The patient was assessed as skin type II. The chart records a previous melanoma. A male patient roughly 75 years of age.
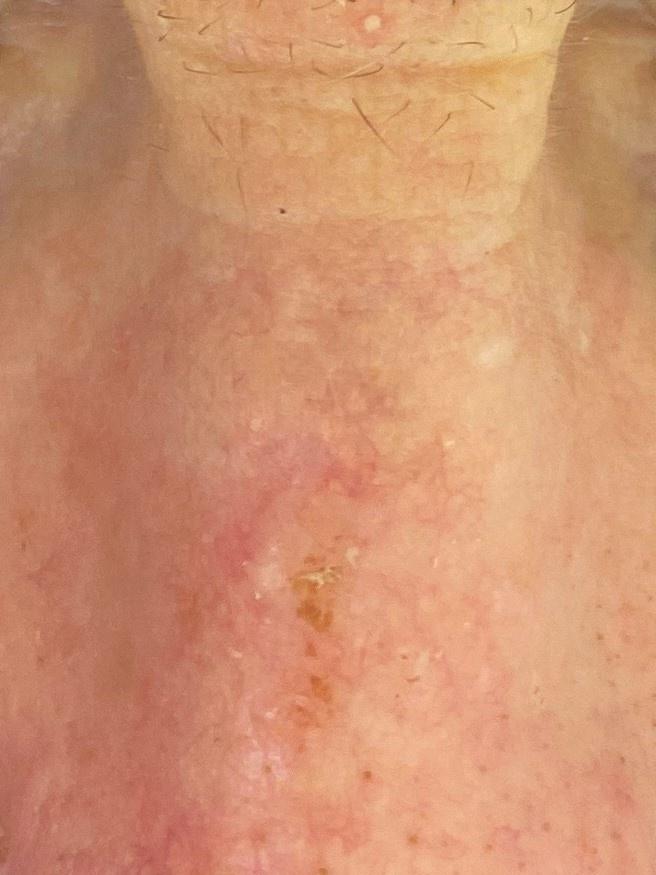The lesion is located on the head or neck.
Biopsy-confirmed as a lesion of adnexal (follicular) origin — a basal cell carcinoma.